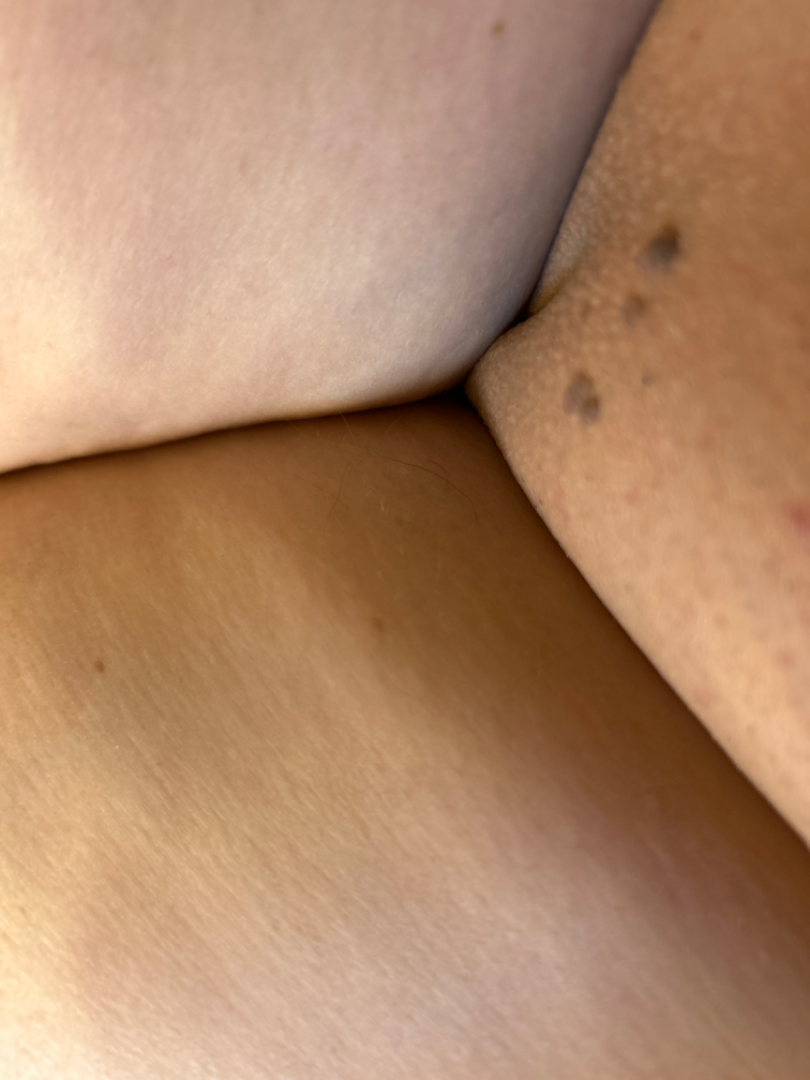  shot_type: at an angle
  differential:
    tied_lead:
      - SK/ISK
      - Condyloma acuminatum